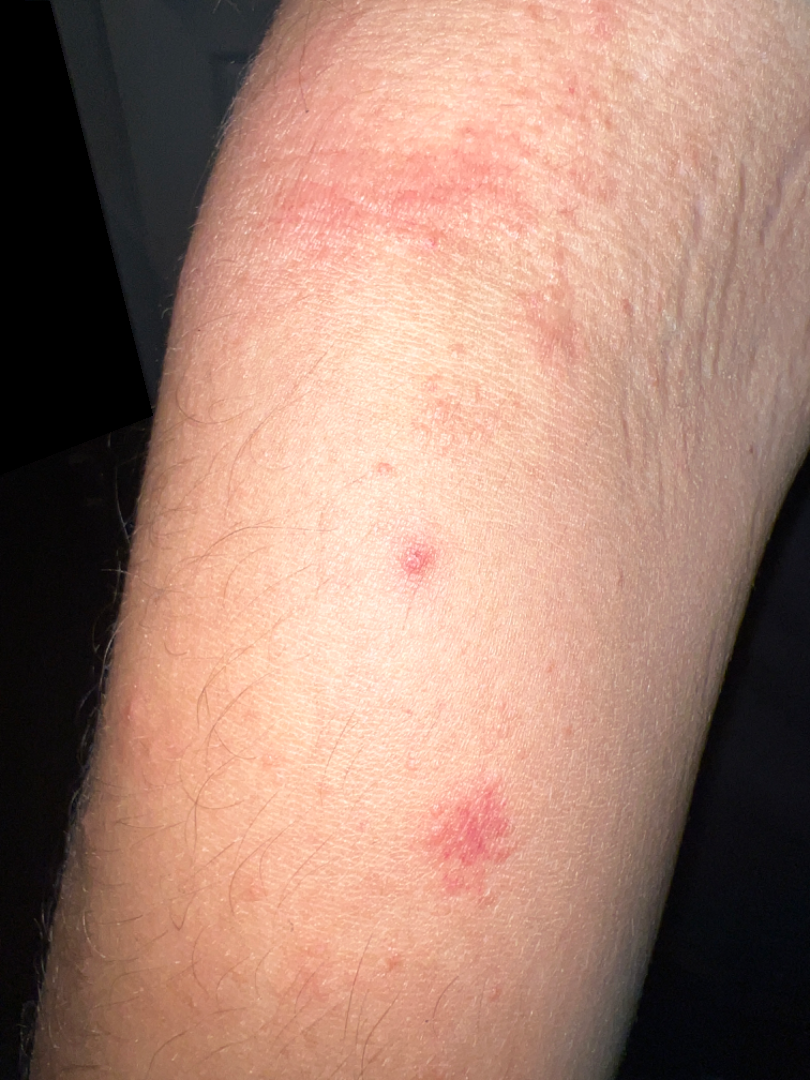patient-reported symptoms: itching and bothersome appearance
self-categorized as: a rash
contributor: male, age 18–29
view: close-up
site: arm
other reported symptoms: none reported
impression: Eczema (weight 0.57); Irritant Contact Dermatitis (weight 0.23); Allergic Contact Dermatitis (weight 0.12); Hypersensitivity (weight 0.08)